The patient is Fitzpatrick phototype III · a male subject aged around 50 · a dermatoscopic image of a skin lesion — 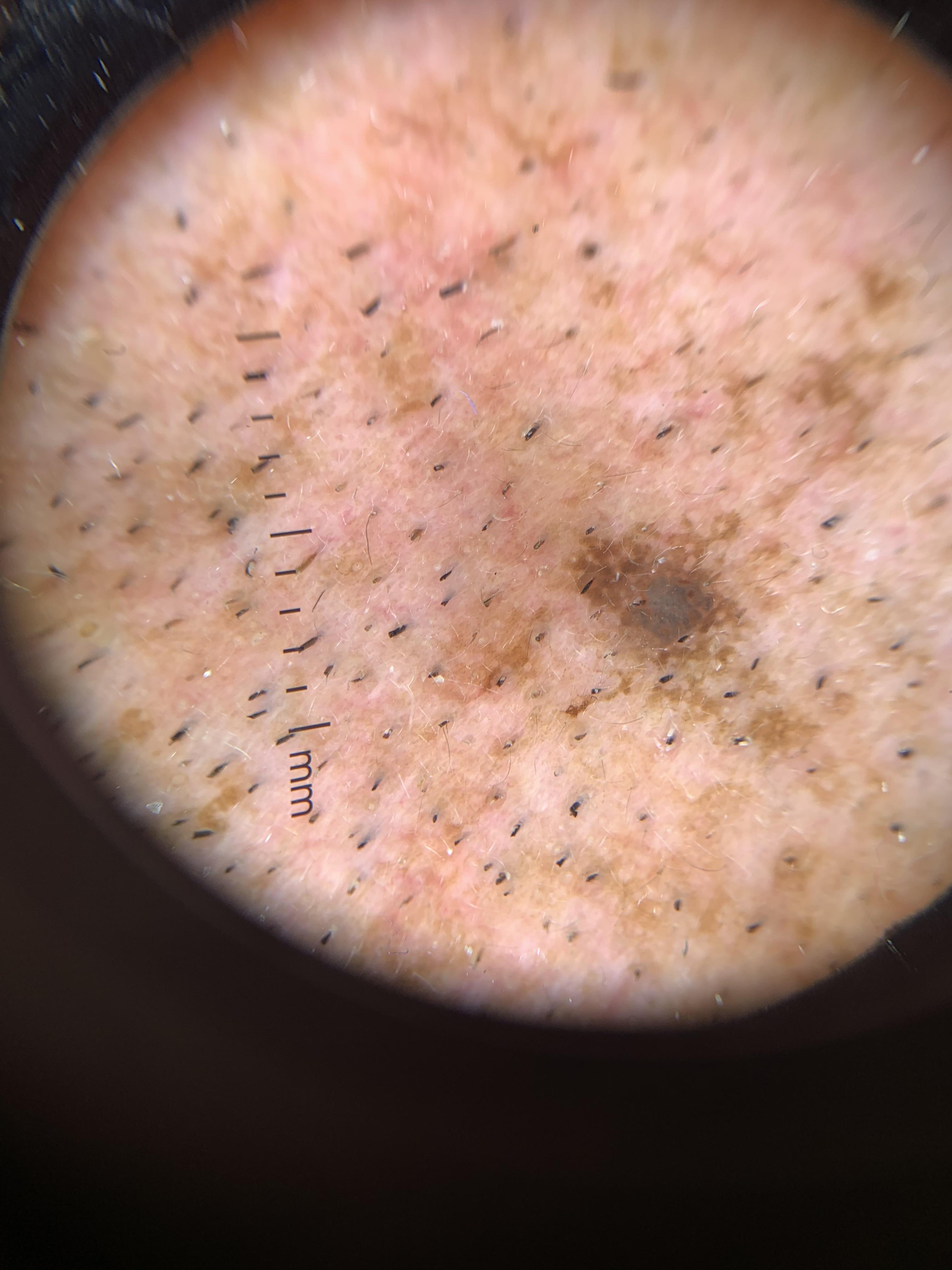location: the head or neck
diagnosis: Seborrheic keratosis (biopsy-proven)